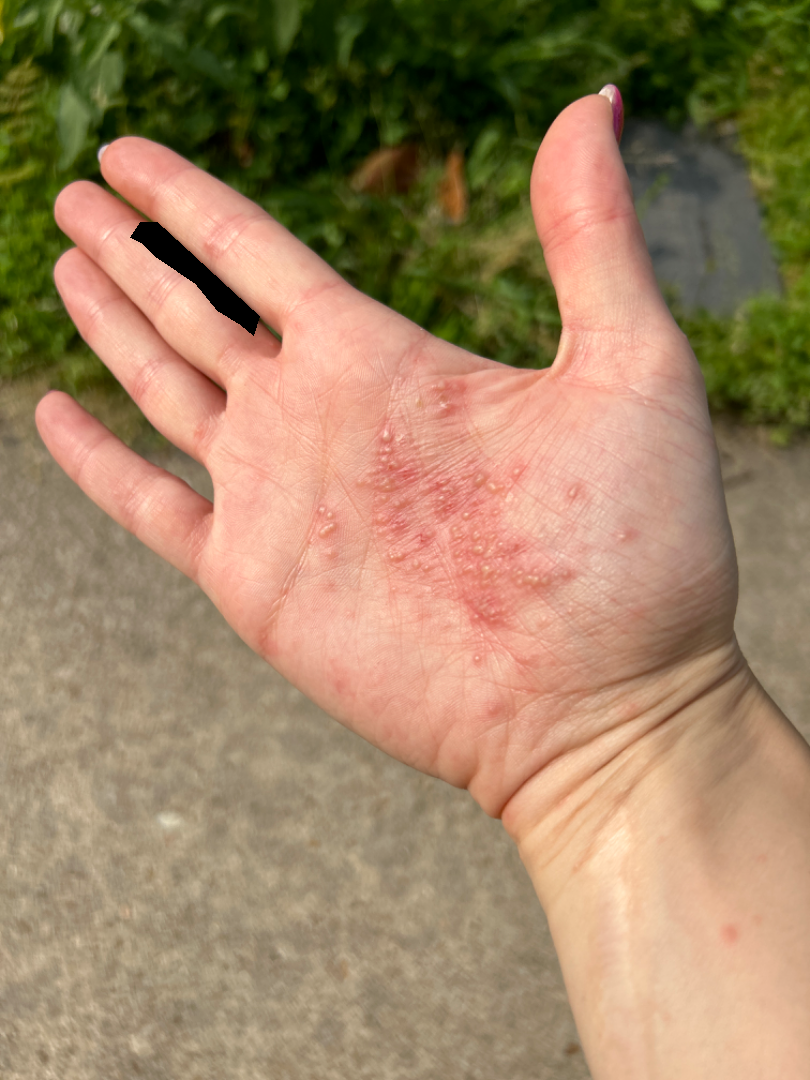No differential diagnosis could be assigned on photographic review.
The affected area is the palm.
The photograph was taken at a distance.